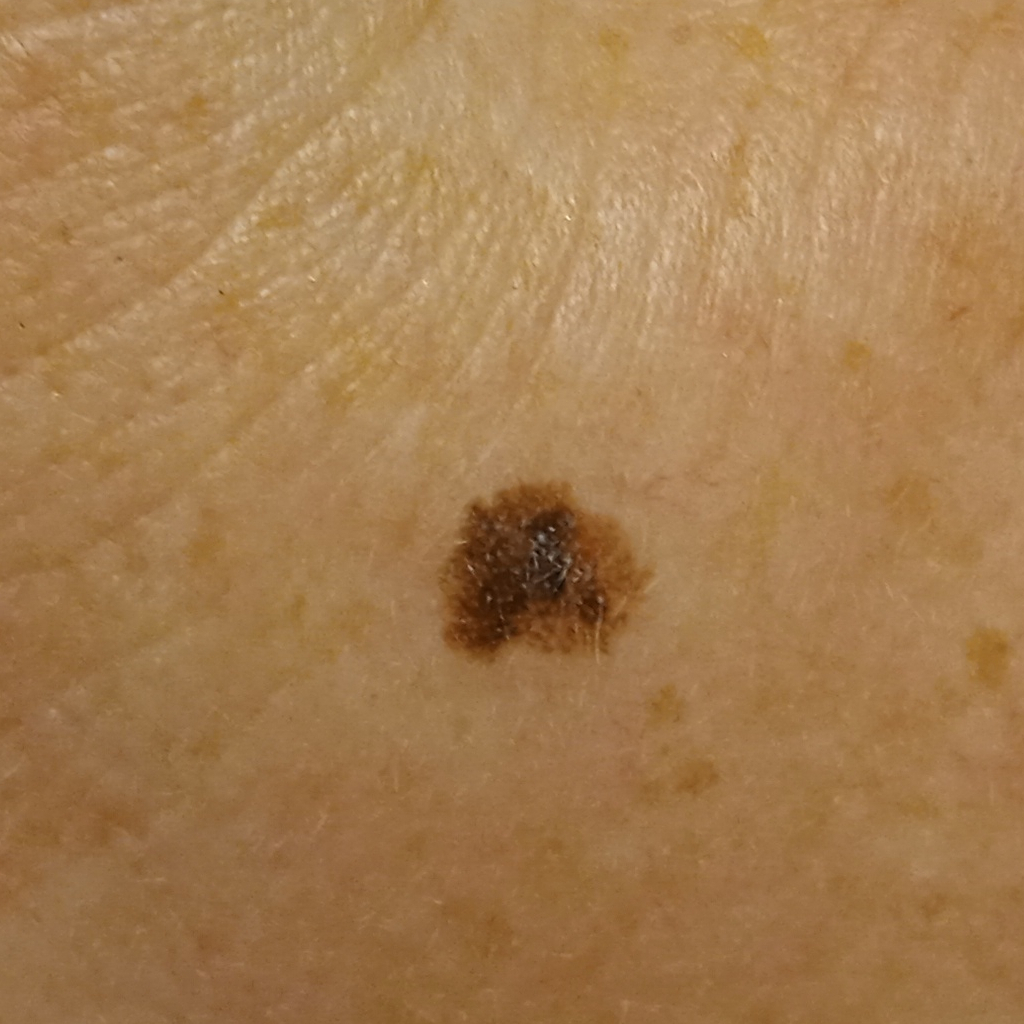Q: What are the relevant risk factors?
A: a personal history of skin cancer, no family history of skin cancer, no immunosuppression
Q: Tell me about the patient.
A: female, aged 50
Q: Why was this imaged?
A: clinical suspicion of melanoma
Q: How does the patient's skin react to sun?
A: skin reddens with sun exposure
Q: What is the patient's nevus burden?
A: a moderate number of melanocytic nevi
Q: What is the imaging modality?
A: clinical photo
Q: What is the anatomic site?
A: the face
Q: How large is the lesion?
A: 7 mm
Q: What did the biopsy show?
A: melanoma (biopsy-proven)